This is a close-up image: 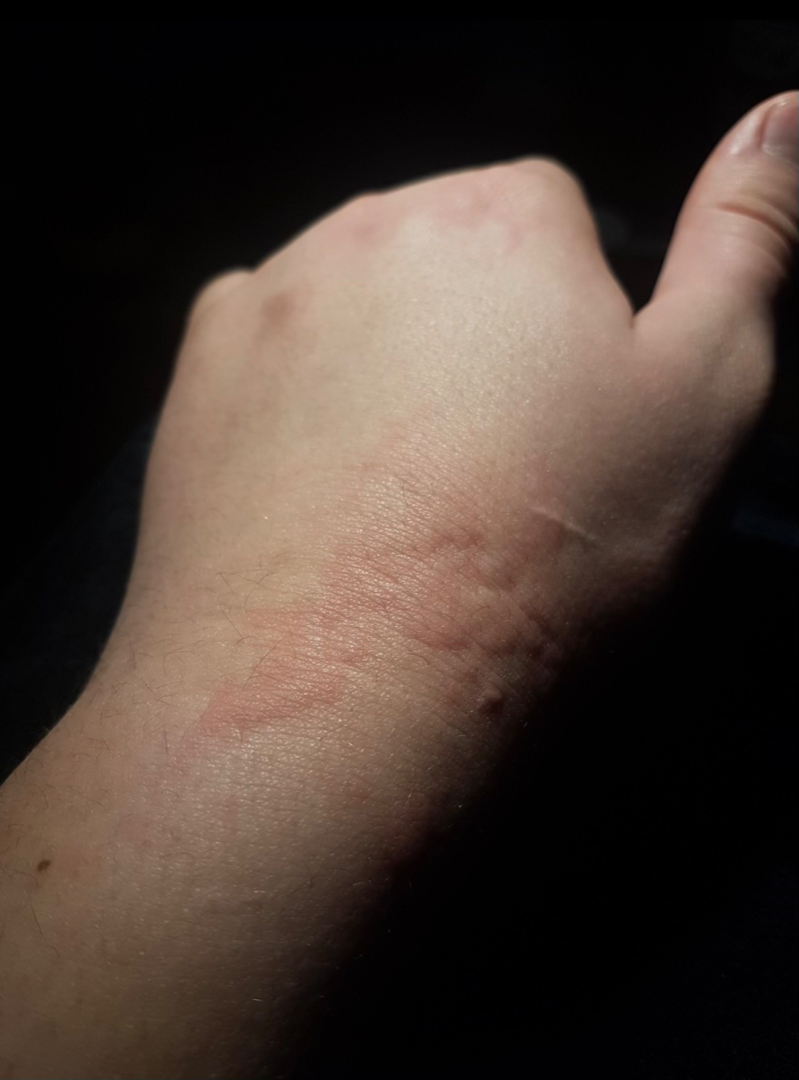Single-reviewer assessment: most consistent with Urticaria; possibly Insect Bite; also consider Allergic Contact Dermatitis.